On a questionnaire the patient reported a personal history of cancer · collected as part of a research study, without a referral diagnosis · a moderate number of moles by the patient's own estimate · the patient says their skin tans without first burning · a clinical close-up of a skin lesion · a male subject aged 65.
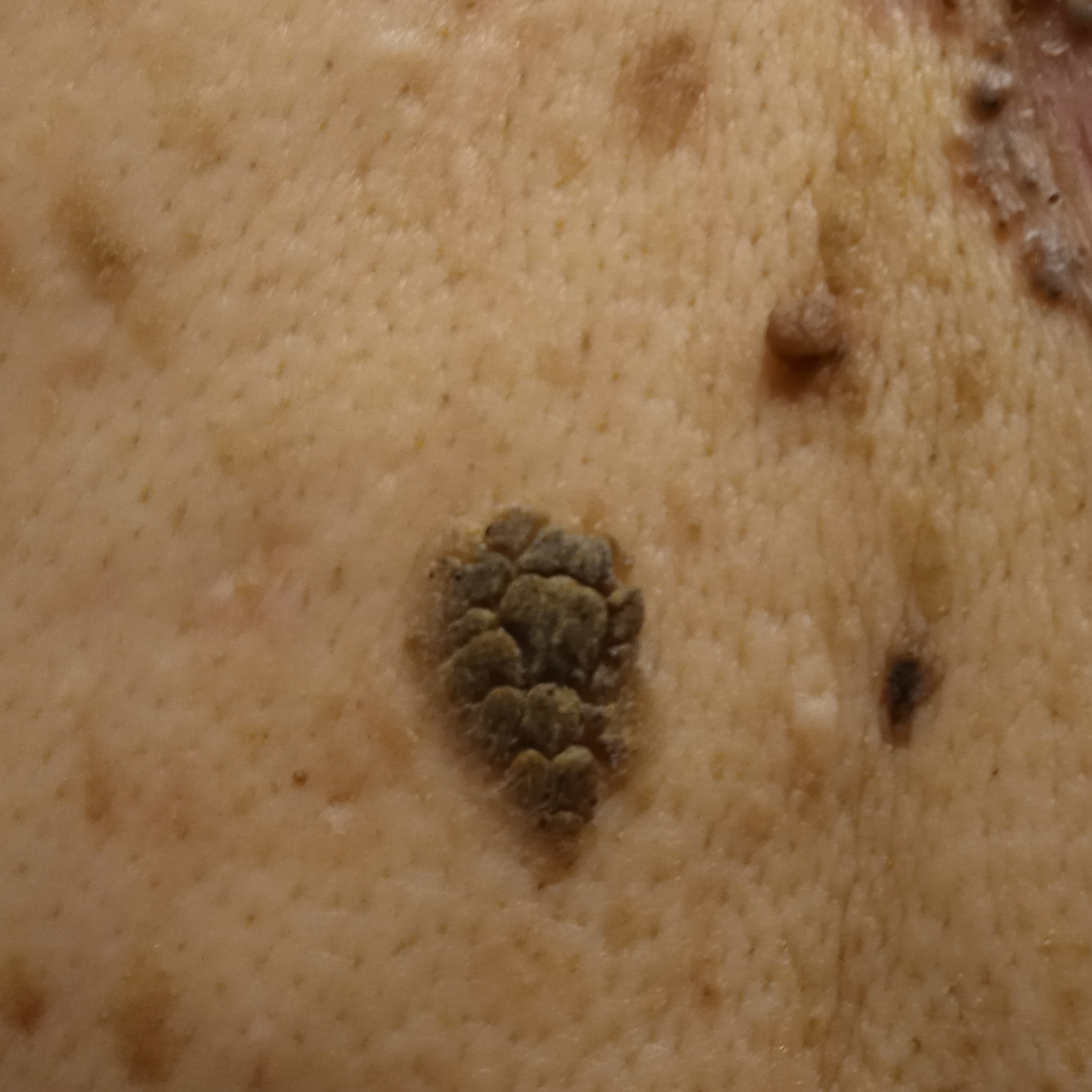The lesion involves the back. The lesion is about 18.8 mm across. The diagnostic impression was a seborrheic keratosis.